A female subject roughly 40 years of age; a dermoscopic close-up of a skin lesion.
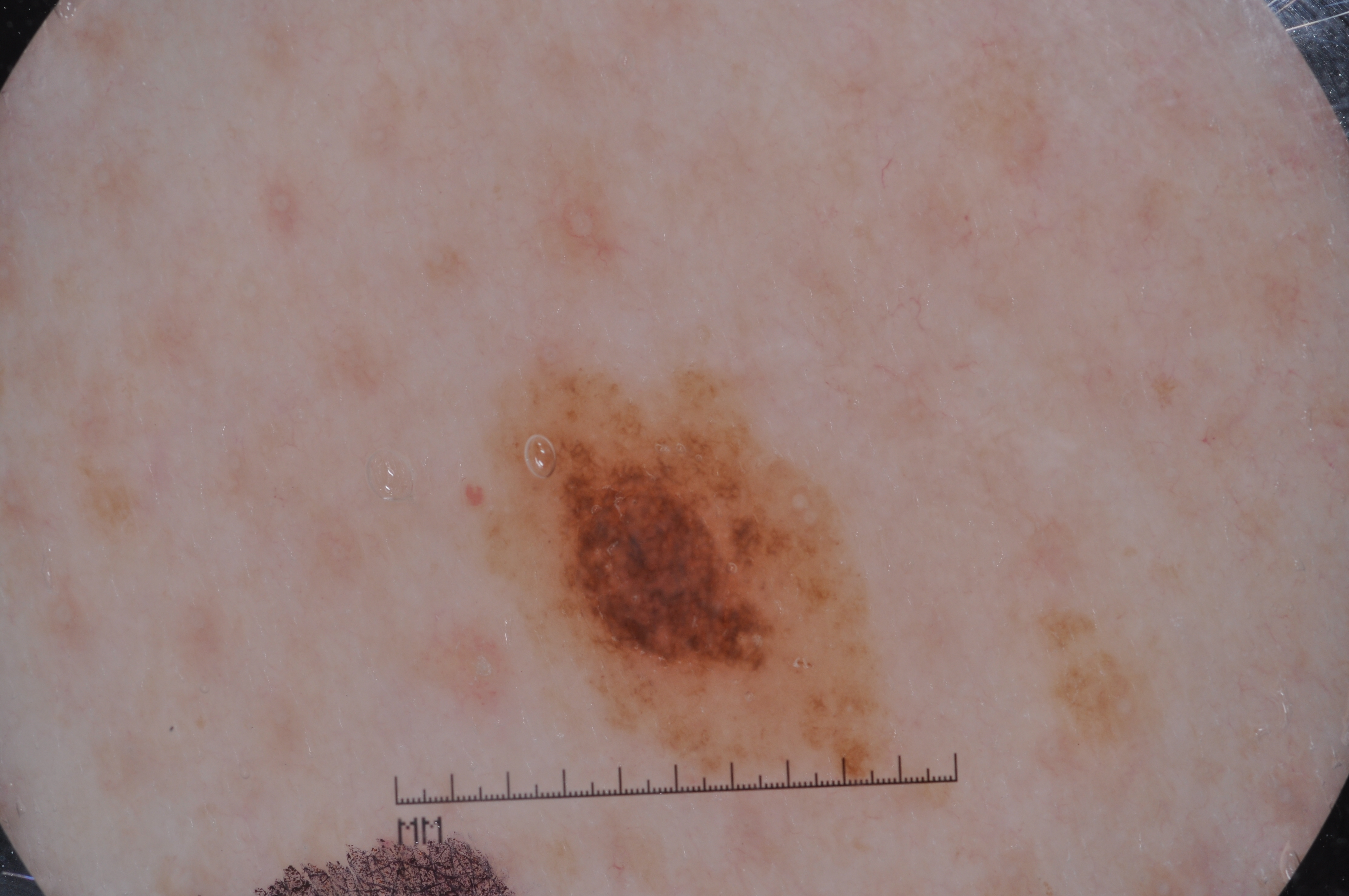lesion size — ~9% of the field
lesion bbox — [495, 365, 875, 770]
dermoscopic pattern — milia-like cysts and pigment network; absent: streaks and negative network
assessment — a melanocytic nevus